The lesion involves the head or neck · close-up view · the contributor is female — 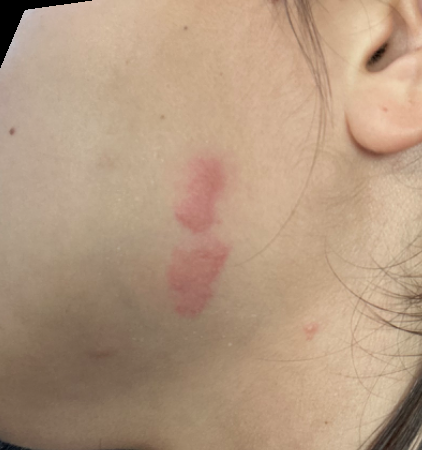On independent review by the dermatologists, Scar Condition (41%); Pseudolymphoma (22%); Urticaria (18%); Cutaneous lupus (18%).